A male subject age 79:
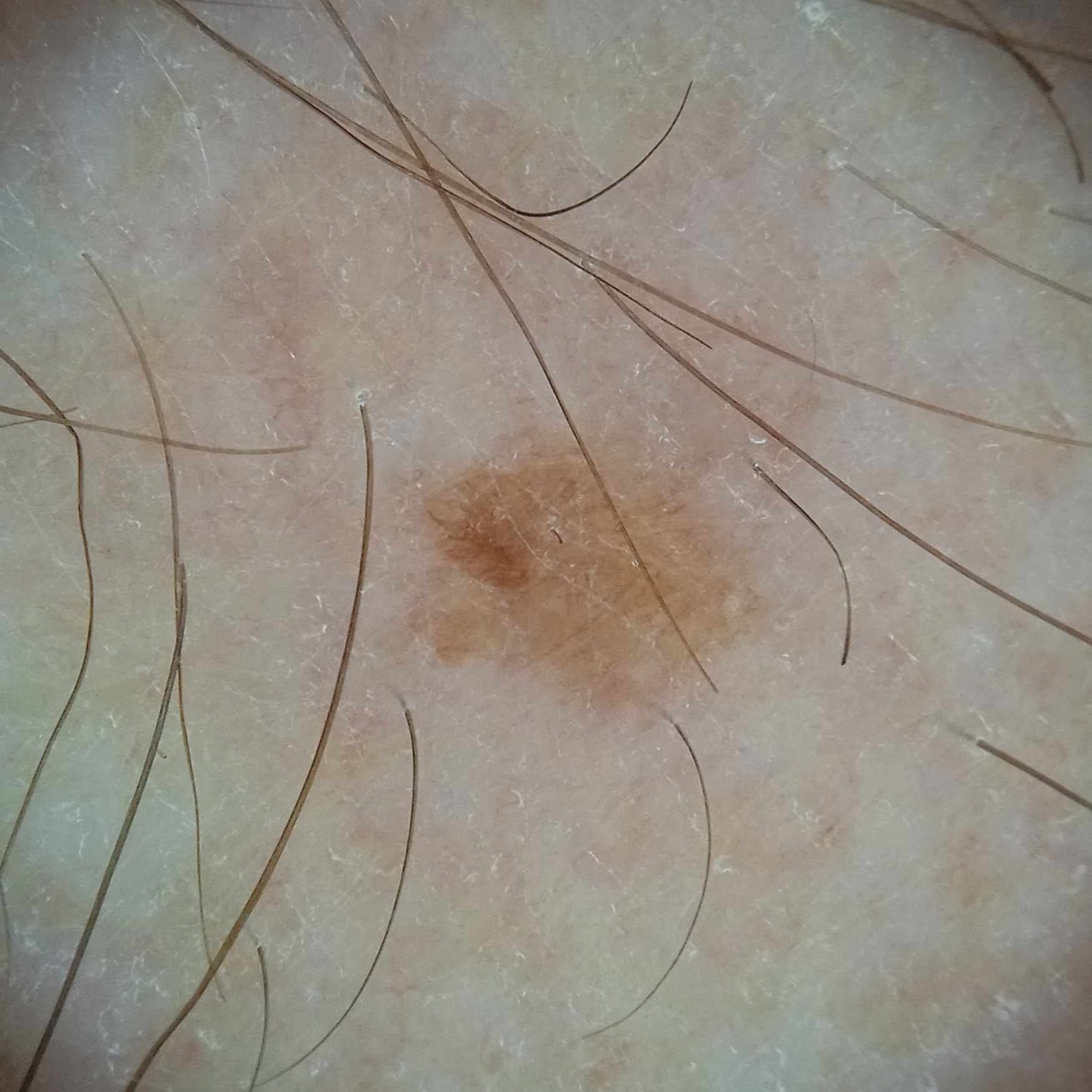Case summary: The lesion is about 4.2 mm across. Assessment: The diagnostic impression was a seborrheic keratosis.